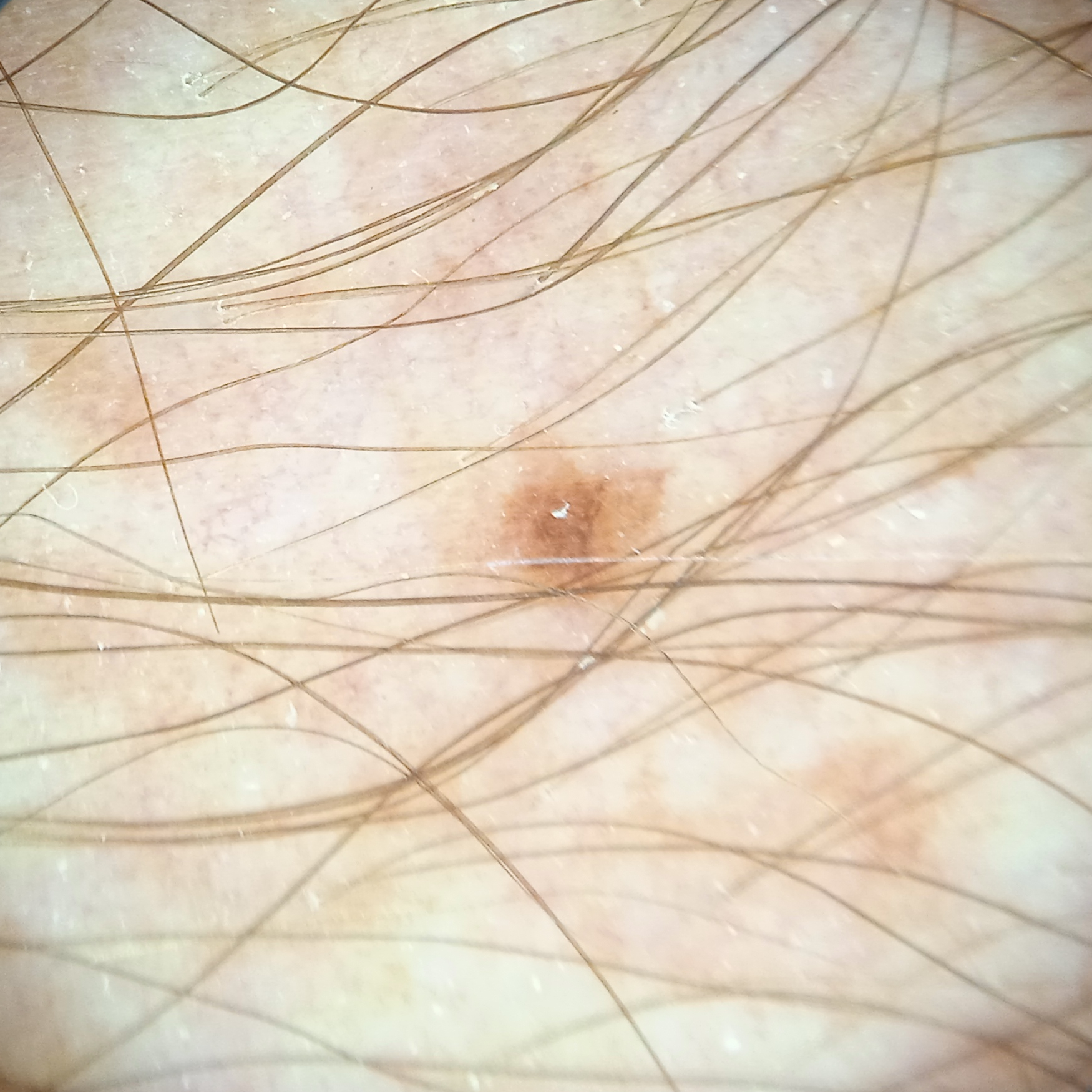A male patient 76 years of age. On a questionnaire the patient reported a personal history of cancer and a personal history of skin cancer. Collected as part of a research study, without a referral diagnosis. Measuring roughly 8.2 mm. The diagnostic impression was a melanocytic nevus.